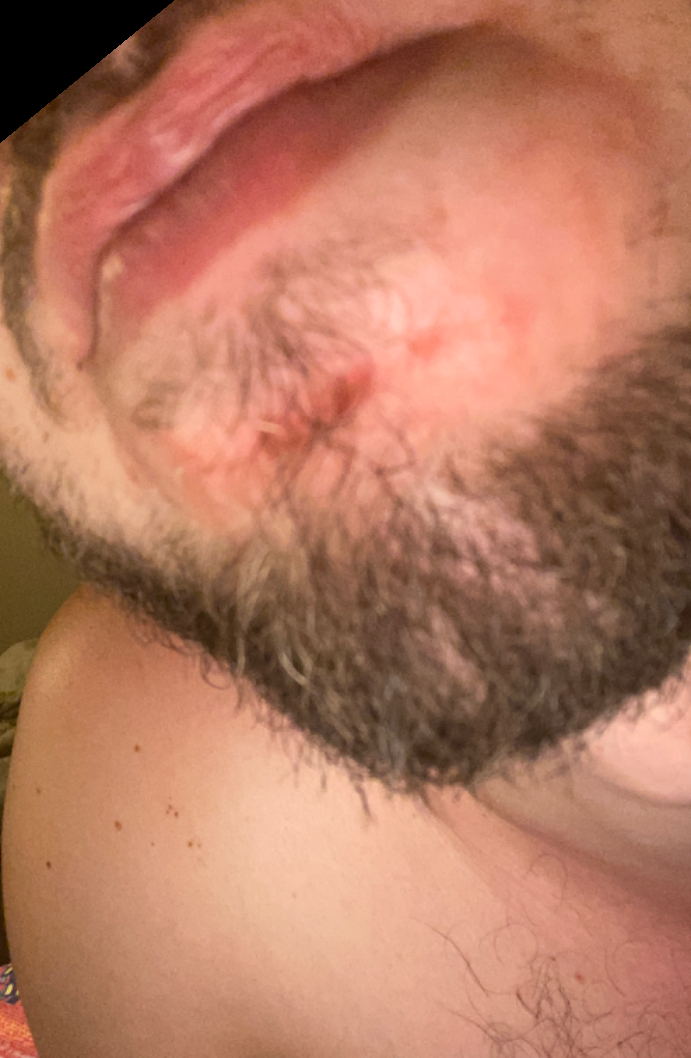Case summary:
* framing · at an angle
* affected area · head or neck
* differential diagnosis · a single dermatologist reviewed the case: the leading impression is Seborrheic Dermatitis; possibly Impetigo; also consider Psoriasis